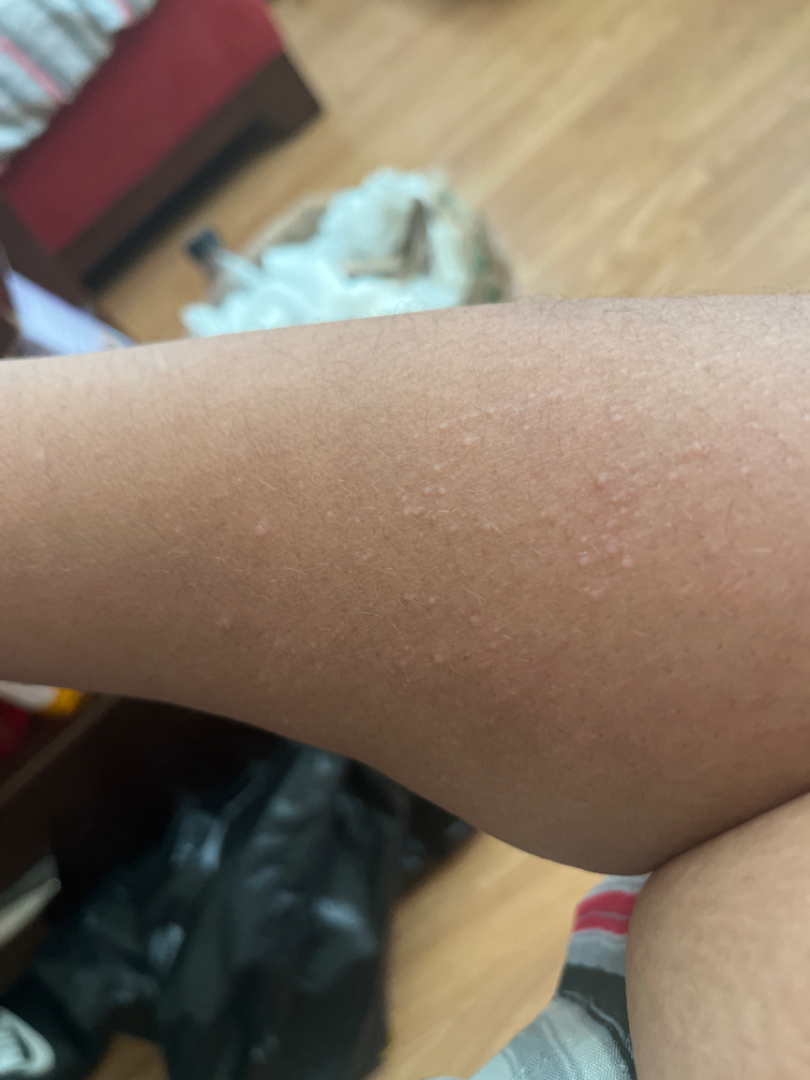Findings:
On remote review of the image: the primary impression is Eczema; with consideration of Lichen nitidus; lower on the differential is Keratosis pilaris.